The photograph was taken at an angle — 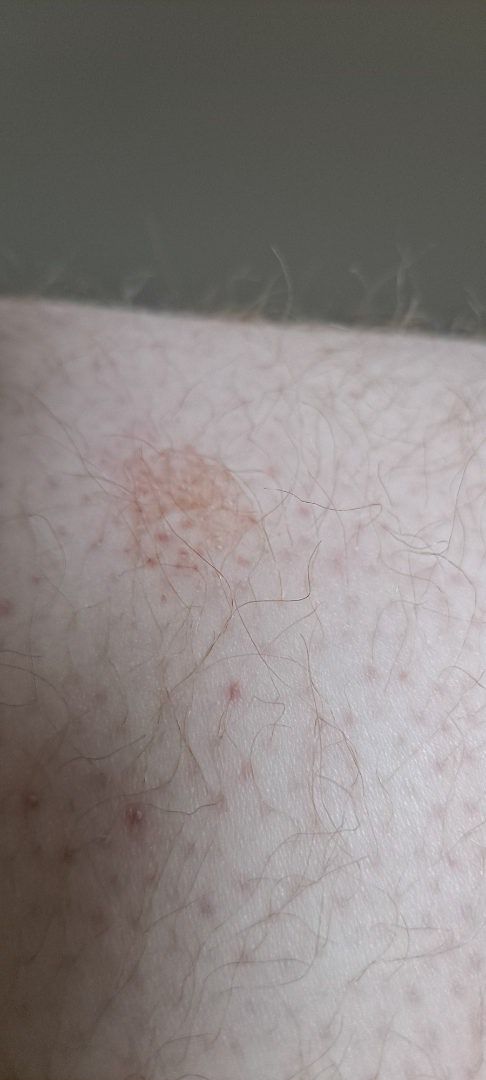No differential diagnosis could be assigned on photographic review.